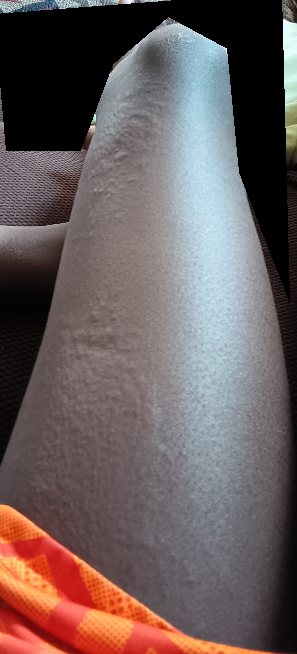No differential diagnosis could be assigned on photographic review. An image taken at a distance. The lesion is associated with itching. The patient described the issue as a rash. The patient reported no systemic symptoms.